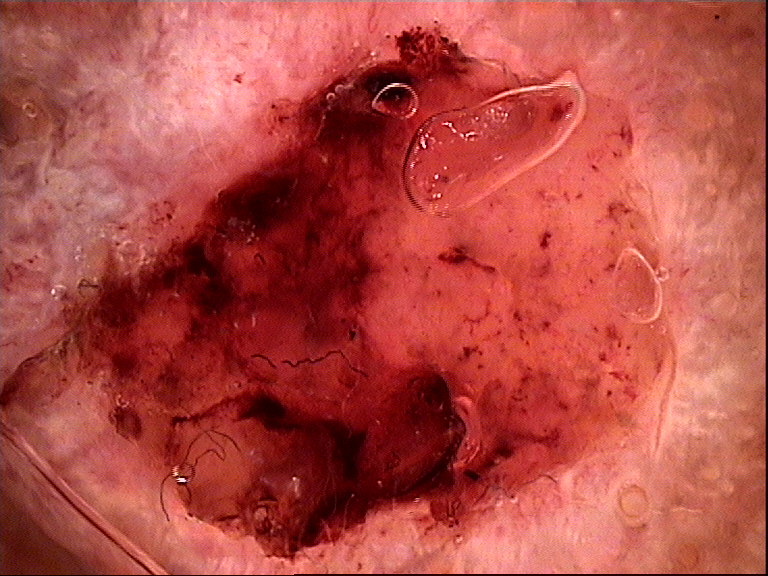<lesion>
  <diagnosis>
    <name>squamous cell carcinoma</name>
    <code>scc</code>
    <malignancy>malignant</malignancy>
    <super_class>non-melanocytic</super_class>
    <confirmation>histopathology</confirmation>
  </diagnosis>
</lesion>